A male subject 79 years old; acquired for a research image collection, with no referral diagnosis:
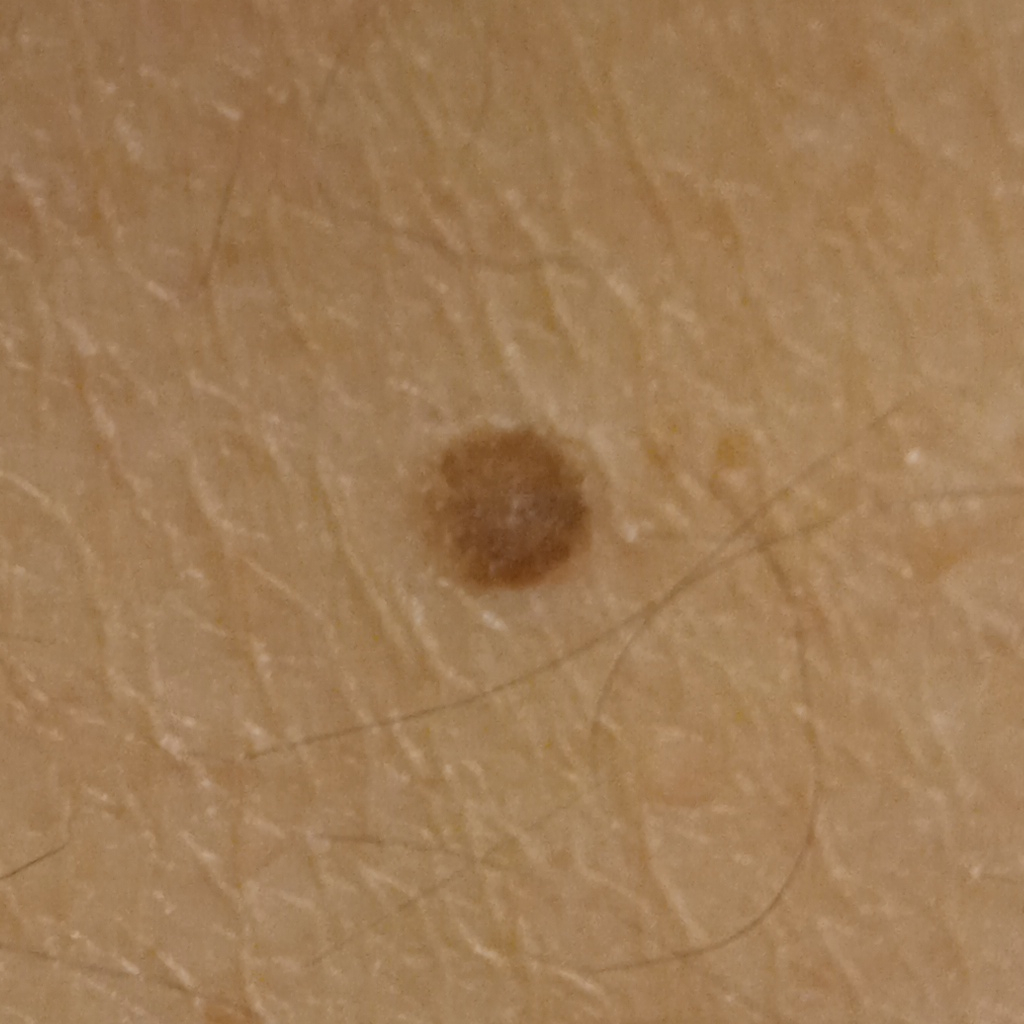Case summary: The lesion measures approximately 5.8 mm. Conclusion: The dermatologists' assessment was a melanocytic nevus.